The patient is 18–29, female; close-up view; the affected area is the leg.
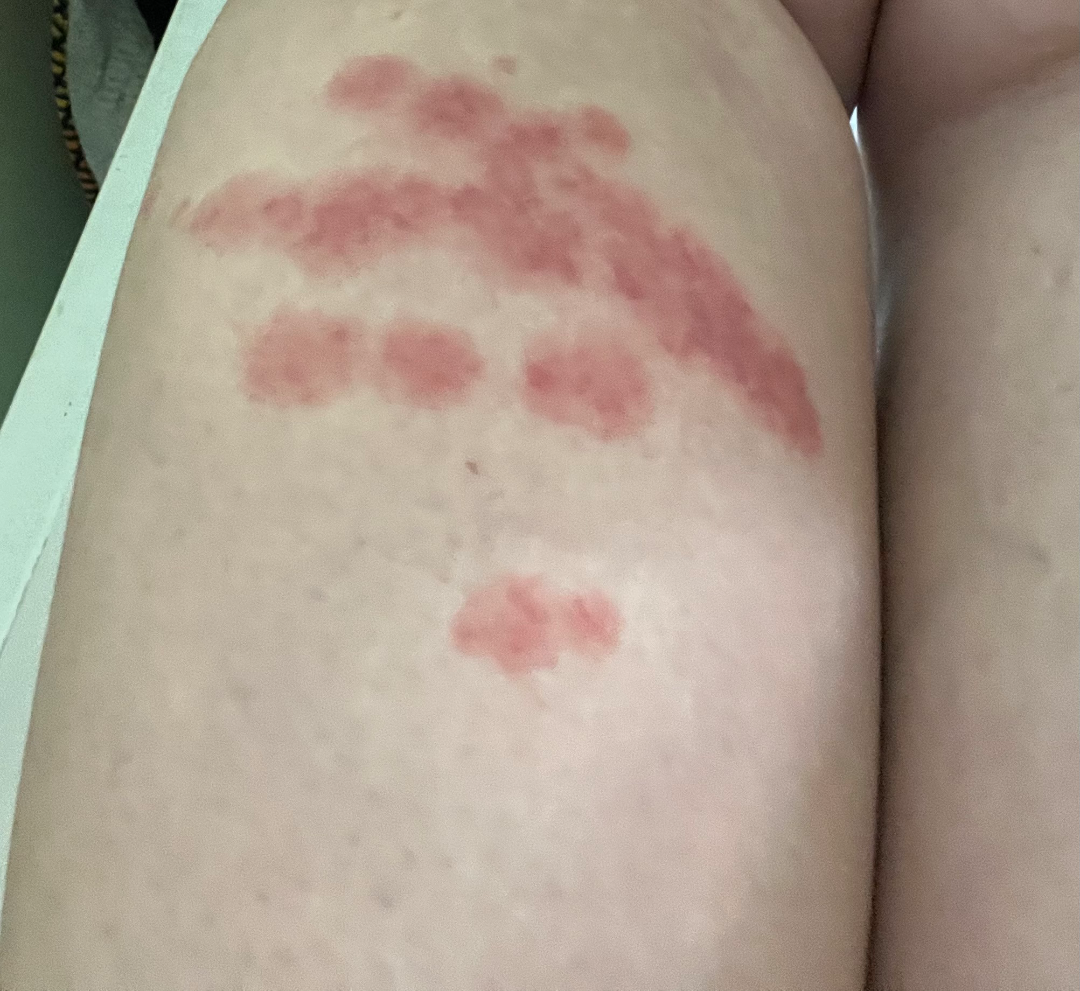The reviewing dermatologist was unable to assign a differential diagnosis from the image. FST III; non-clinician graders estimated Monk Skin Tone 2 or 3 (two reviewer pools). The lesion is associated with burning and itching. The patient considered this a rash. The patient notes the lesion is raised or bumpy. The patient notes the condition has been present for less than one week.